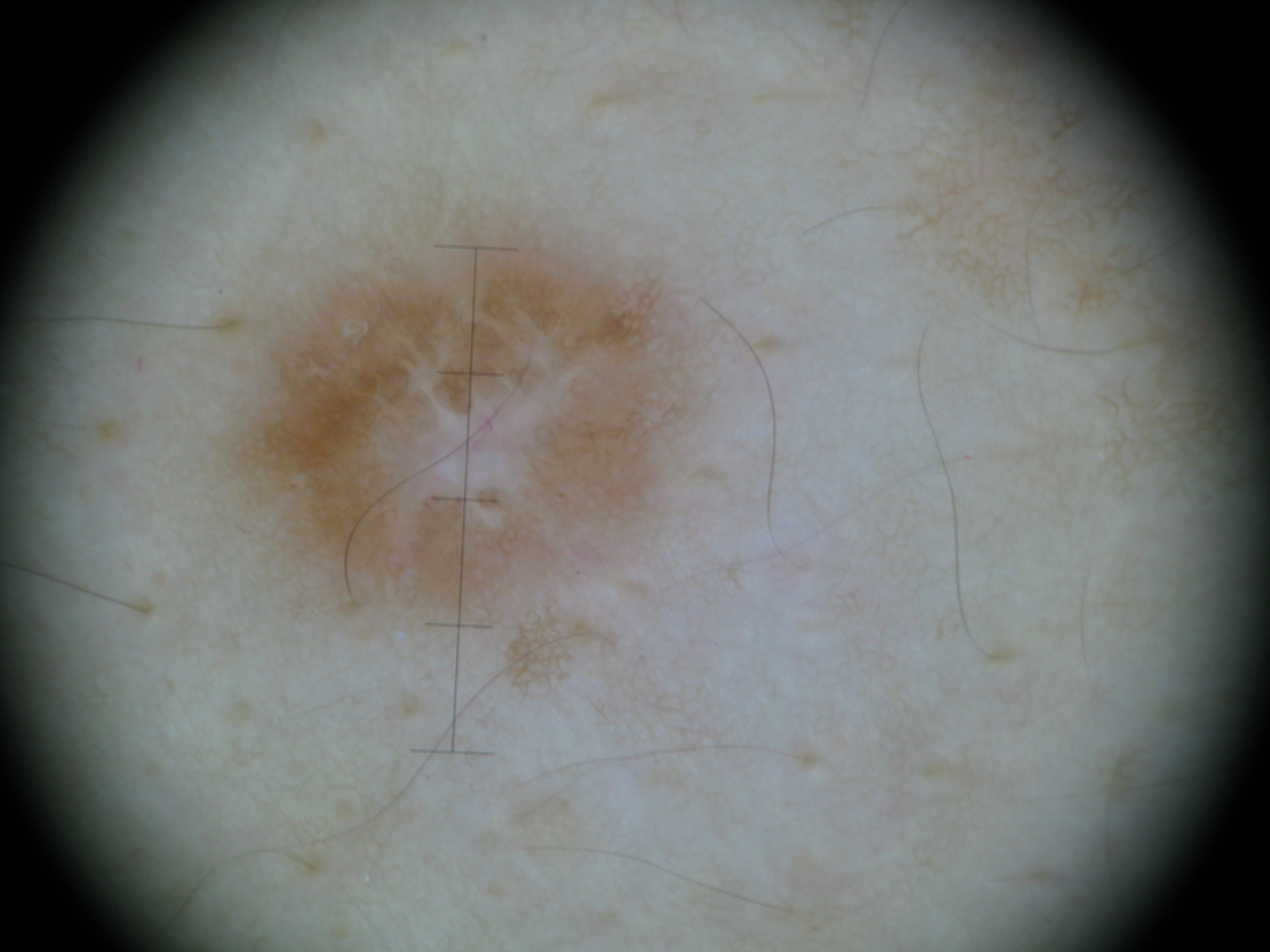Case: A dermoscopic photograph of a skin lesion. Conclusion: The diagnostic label was a fibro-histiocytic lesion — a dermatofibroma.